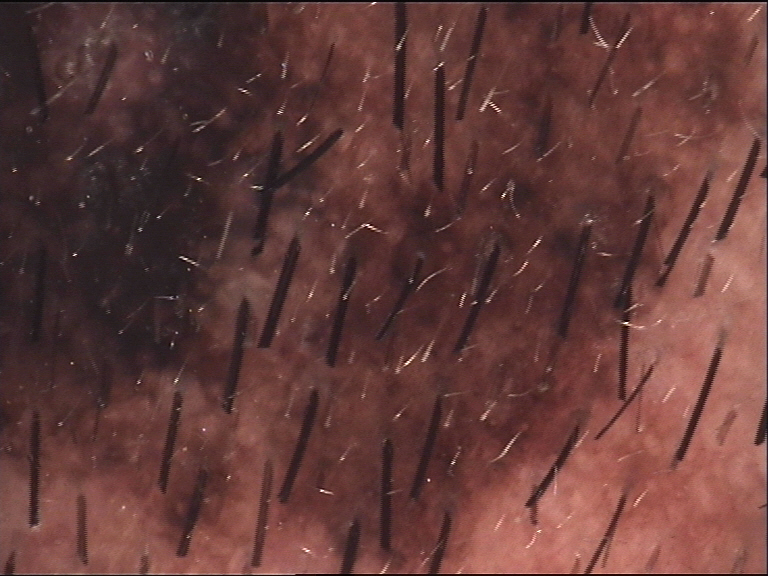Case: A dermoscopic photograph of a skin lesion. The architecture is that of a banal lesion. Impression: The diagnostic label was a congenital compound nevus.